The contributor is female. This is a close-up image. The arm, back of the hand, leg and head or neck are involved:
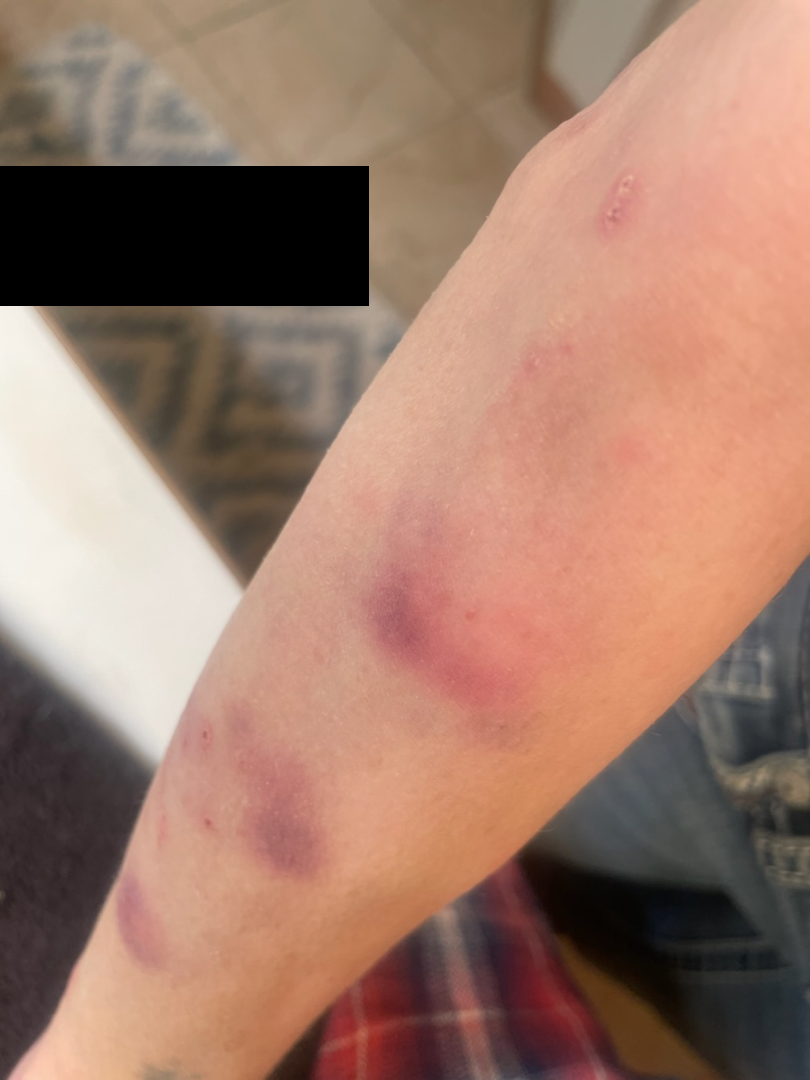The case was indeterminate on photographic review.